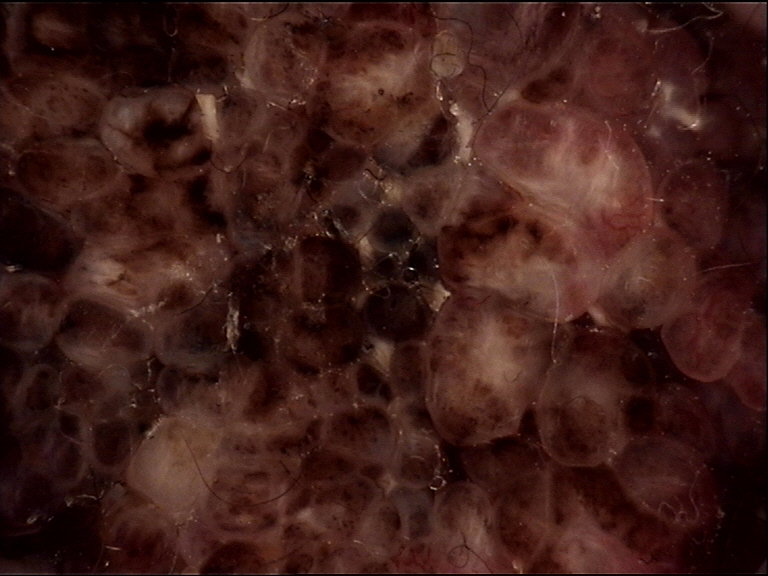A dermatoscopic image of a skin lesion. The morphology is that of a banal lesion. The diagnostic label was a congenital compound nevus.